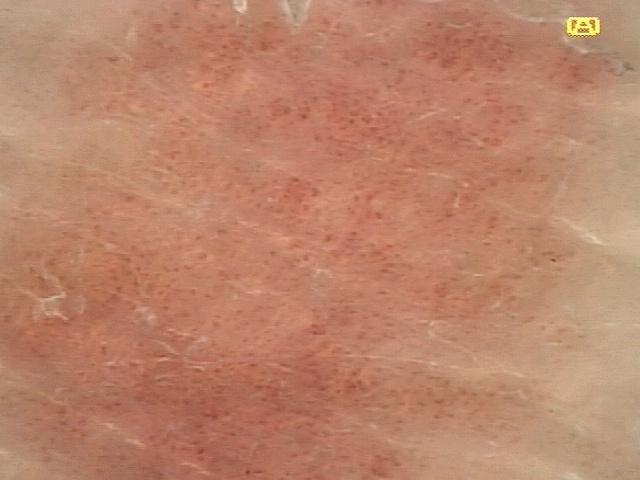Summary:
Dermoscopy of a skin lesion. Skin type II. A male patient in their 70s. The lesion is on the head or neck.
Assessment:
The diagnostic impression was an epidermal lesion — a solar or actinic keratosis.